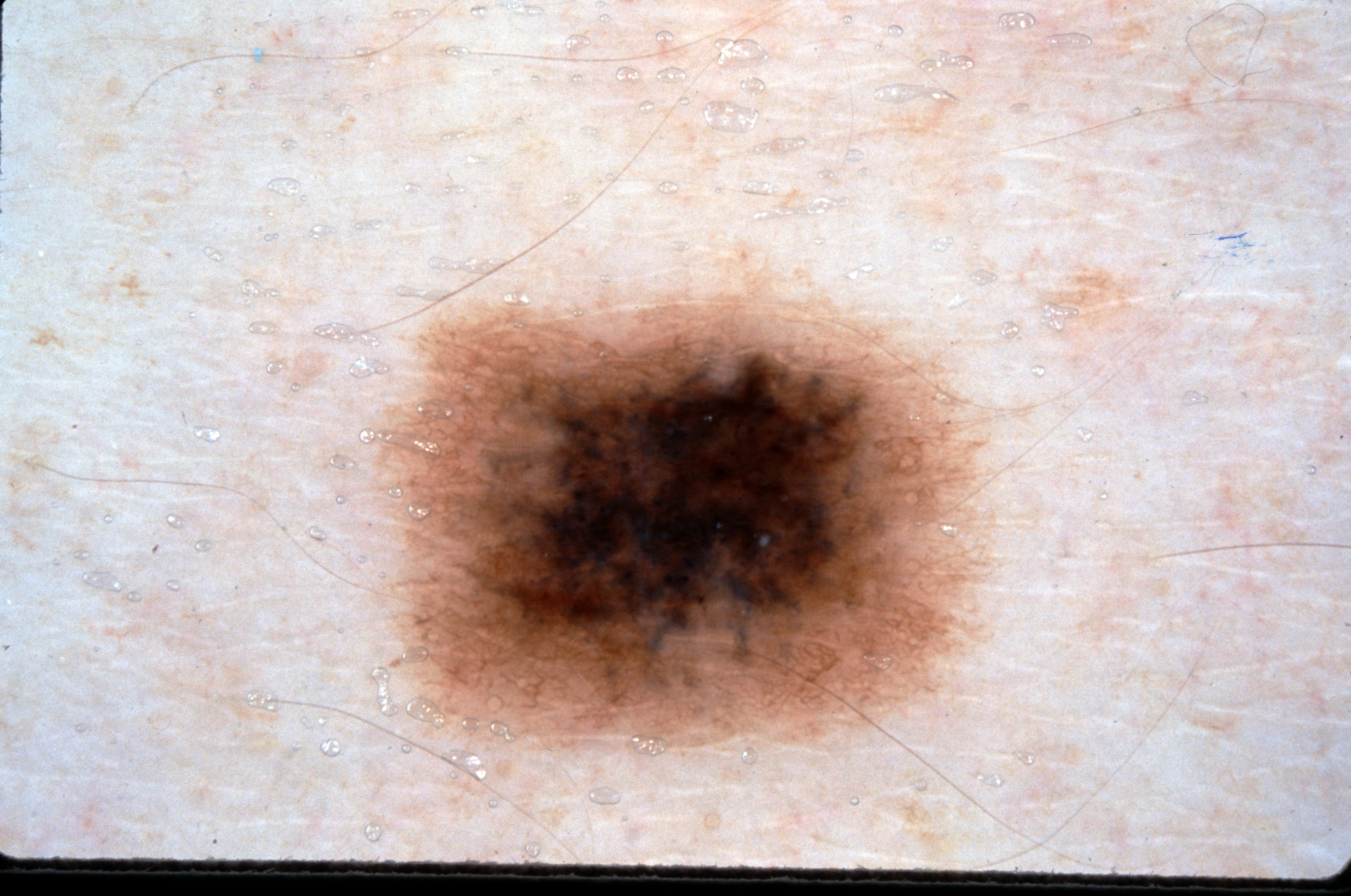A dermatoscopic image of a skin lesion.
A female patient roughly 35 years of age.
The visible lesion spans left=364, top=277, right=991, bottom=766.
A moderately sized lesion.
Dermoscopic examination shows pigment network.
The lesion was assessed as a melanocytic nevus, a benign skin lesion.